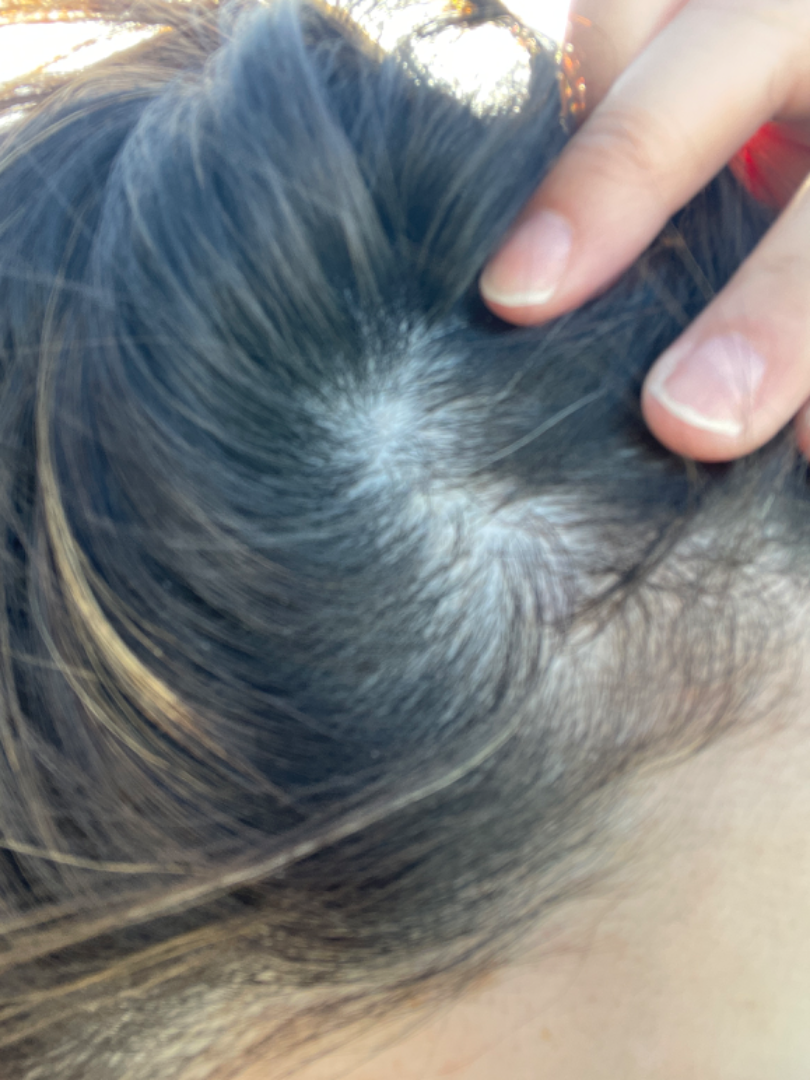No clear dermatological pathology was apparent in the photograph.